An image taken at an angle.
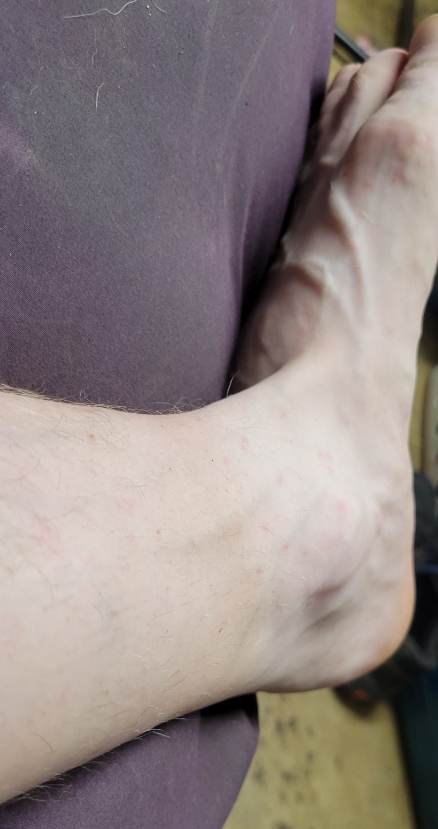Skin tone: Fitzpatrick II.
The impression was split between Viral Exanthem, Folliculitis and Insect Bite.